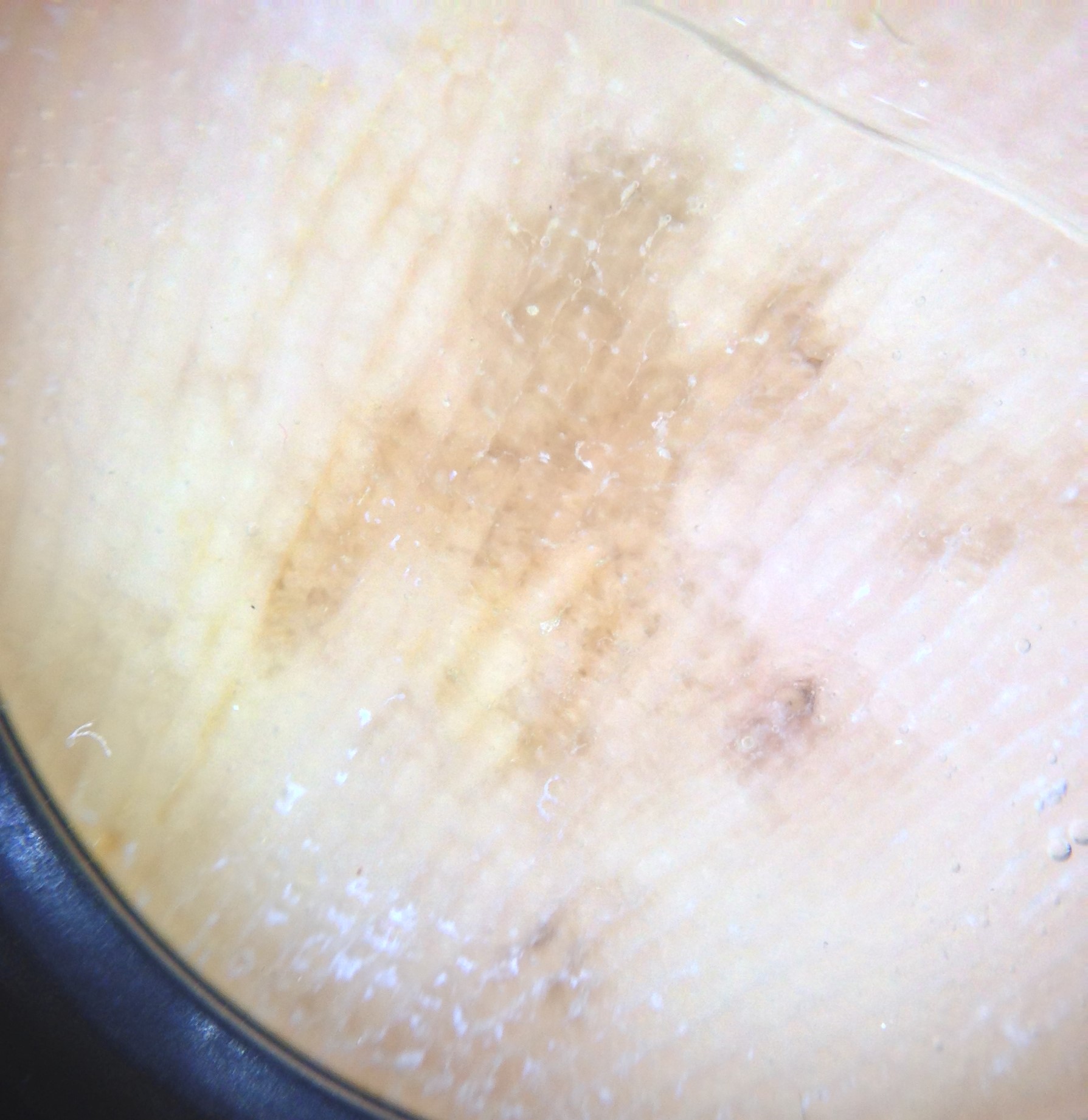image type=dermatoscopy; class=acral lentiginous melanoma (biopsy-proven).